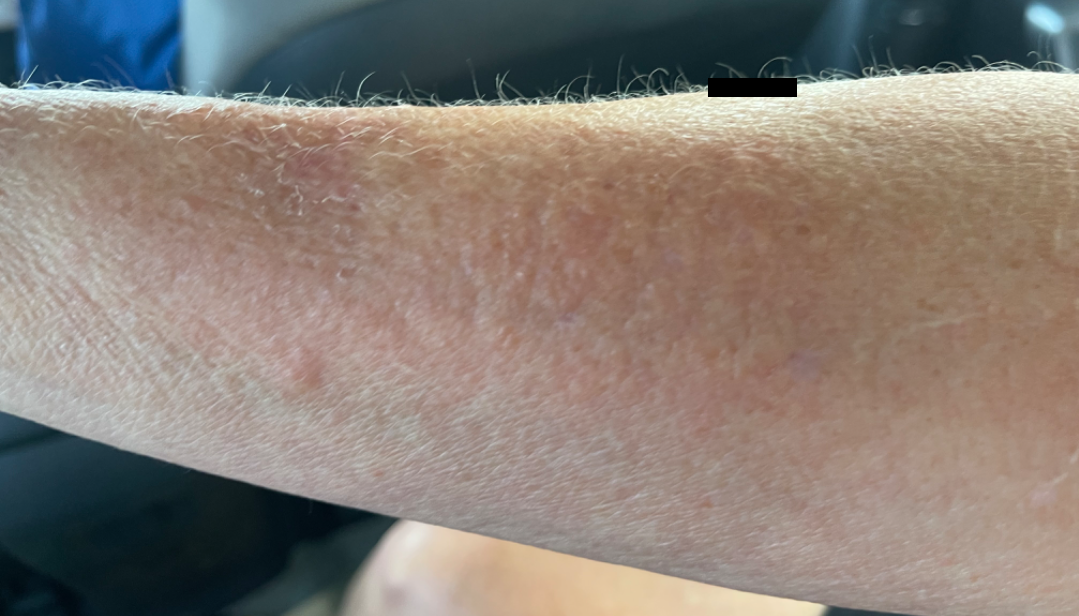The reviewing dermatologist was unable to assign a differential diagnosis from the image.
FST III.
Texture is reported as raised or bumpy.
Reported lesion symptoms include enlargement and itching.
A close-up photograph.
Reported duration is one to four weeks.
The patient described the issue as a rash.